A dermoscopic close-up of a skin lesion.
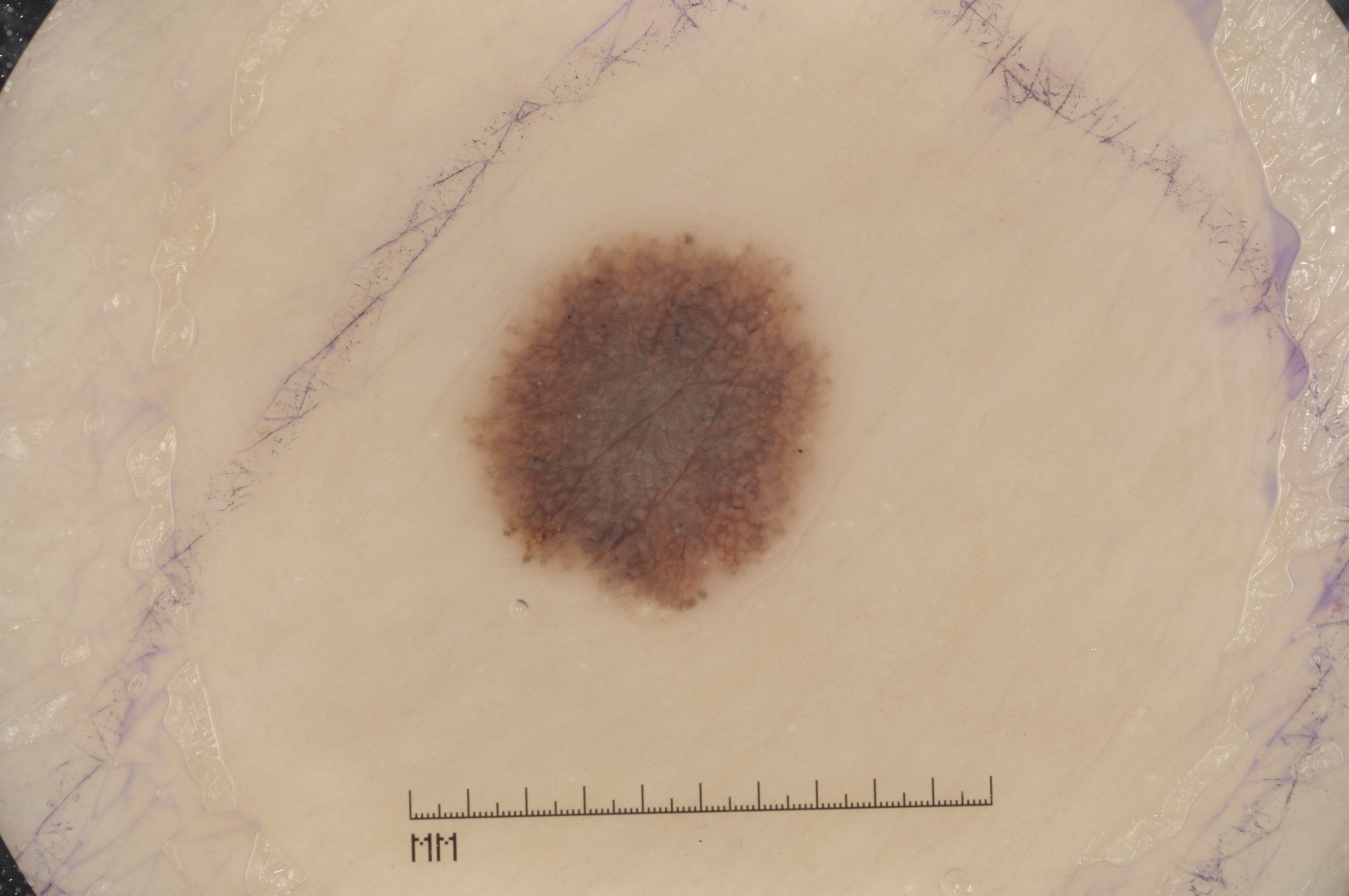In (x1, y1, x2, y2) order, the lesion is bounded by <bbox>474, 231, 832, 609</bbox>. A moderately sized lesion. Dermoscopy demonstrates pigment network and milia-like cysts. Diagnosed as a melanocytic nevus, a benign skin lesion.